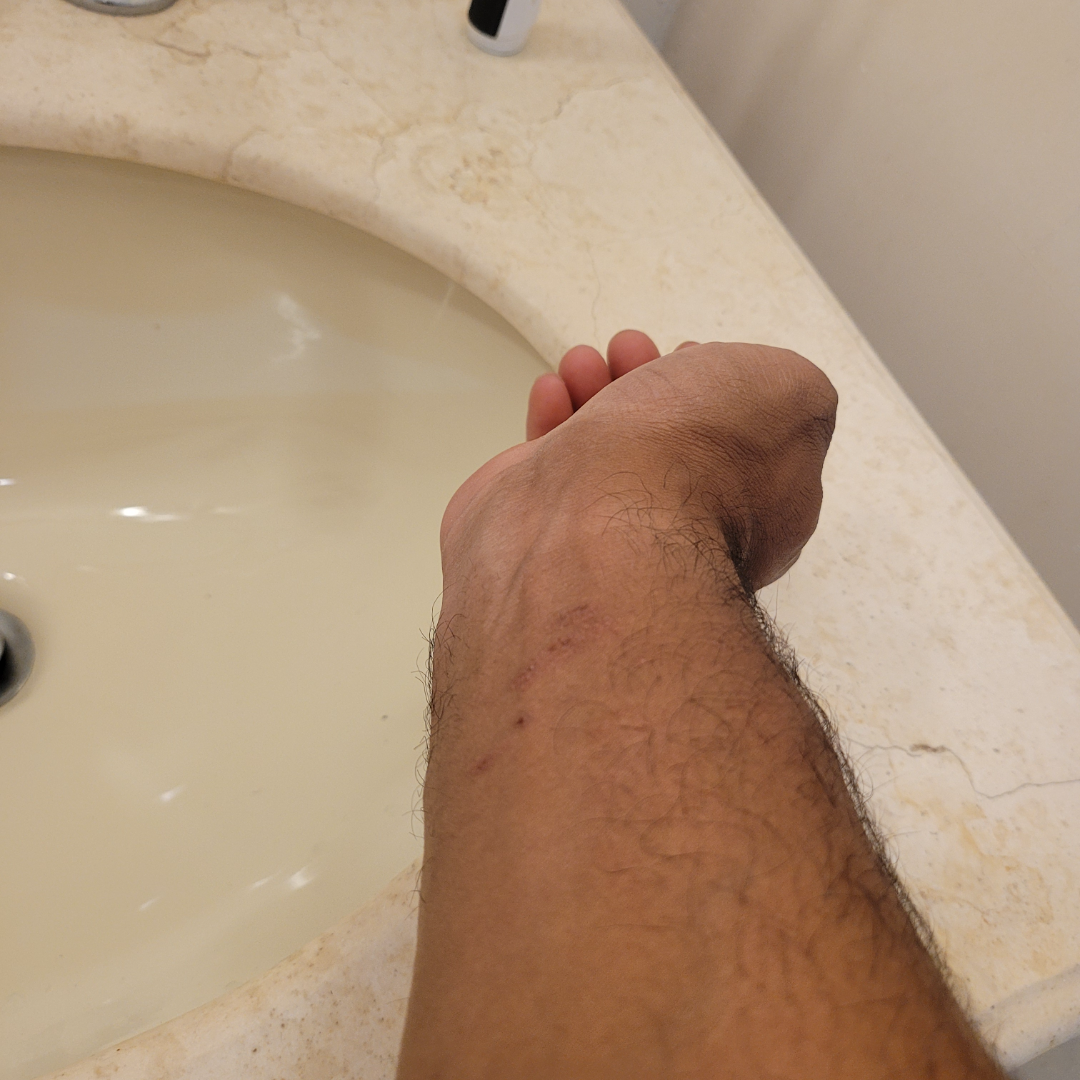Notes:
* assessment: unable to determine
* patient describes the issue as: a rash
* present for: less than one week
* systemic symptoms: none reported
* lesion symptoms: itching
* view: at an angle
* skin tone: FST V
* affected area: leg and arm
* subject: male, age 30–39
* texture: raised or bumpy